A clinical close-up photograph of a skin lesion · by history, alcohol use, pesticide exposure, and prior skin cancer (patient or family) · a male subject in their 50s · the patient is Fitzpatrick phototype II — 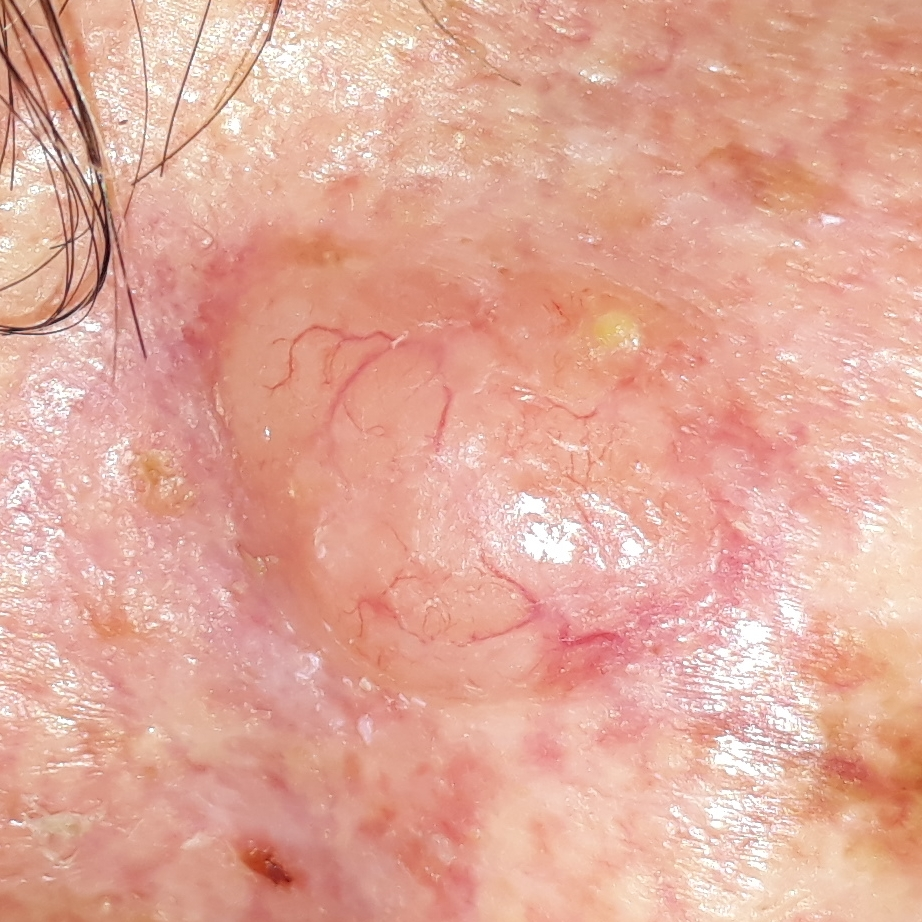<case>
  <lesion_location>an ear</lesion_location>
  <lesion_size>
    <diameter_1_mm>15.0</diameter_1_mm>
    <diameter_2_mm>10.0</diameter_2_mm>
  </lesion_size>
  <symptoms>
    <present>pain, growth, elevation, itching, bleeding</present>
  </symptoms>
  <diagnosis>
    <name>basal cell carcinoma</name>
    <code>BCC</code>
    <malignancy>malignant</malignancy>
    <confirmation>histopathology</confirmation>
  </diagnosis>
</case>